A dermoscopy image of a single skin lesion: 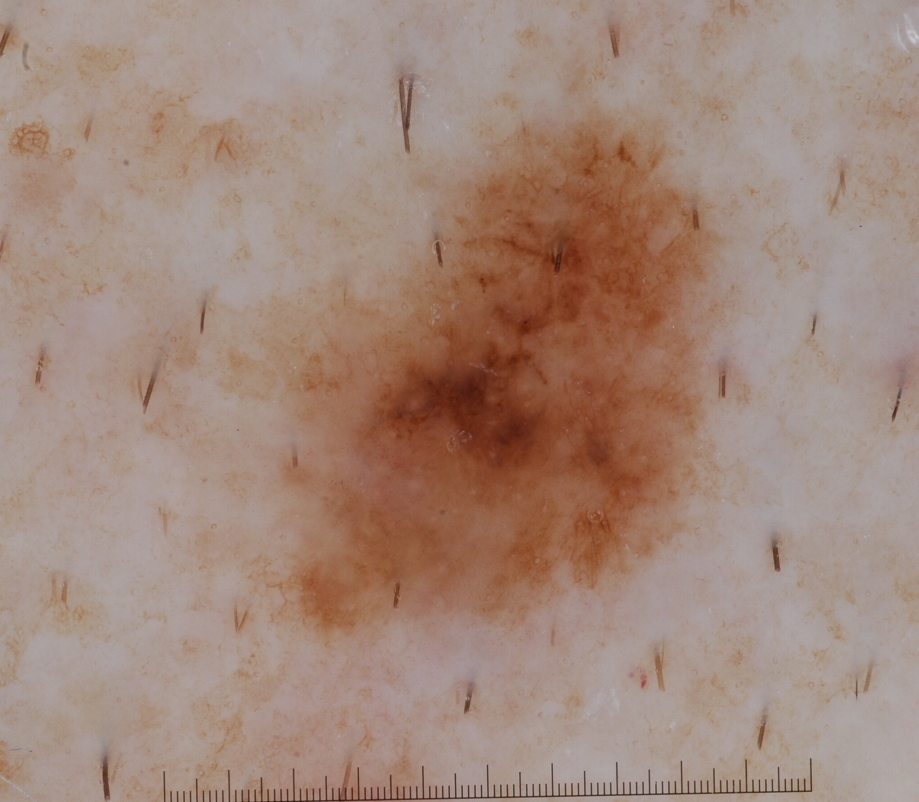Lesion location: <bbox>216, 63, 746, 649</bbox>. The biopsy diagnosis was a melanoma.